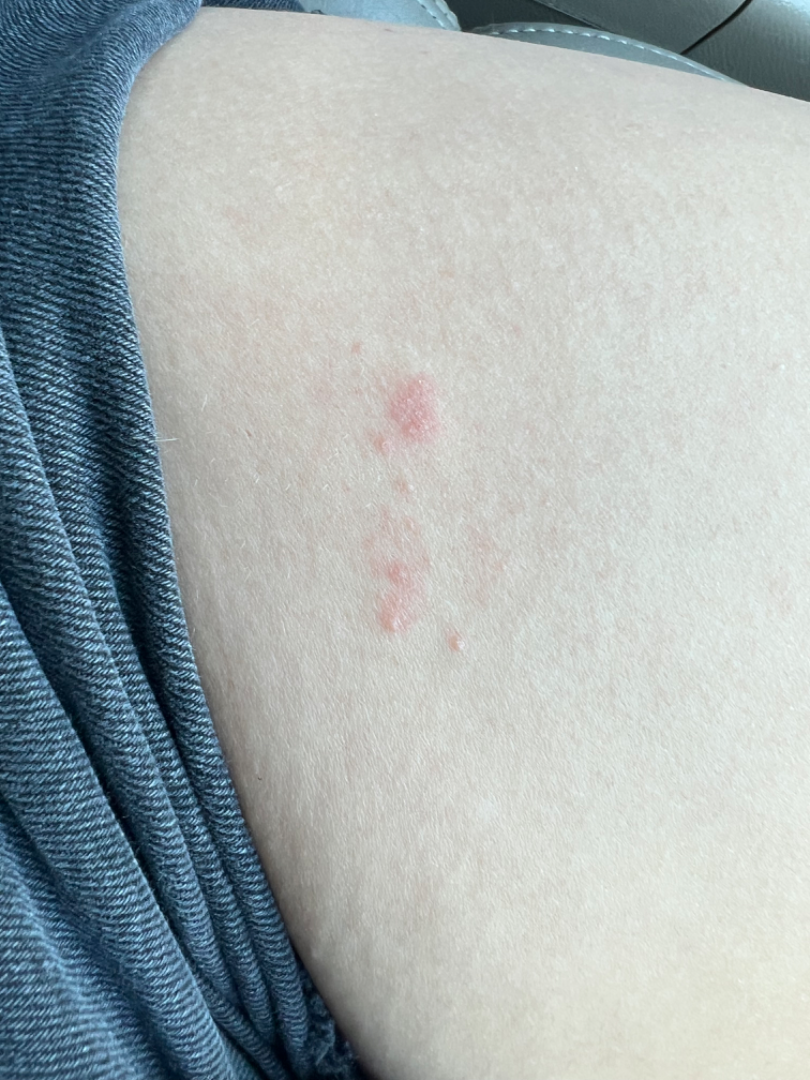History: Located on the leg. Female contributor, age 18–29. This is a close-up image. Impression: On remote review of the image: Folliculitis, Allergic Contact Dermatitis and Herpes Simplex were considered with similar weight.